A dermatoscopic image of a skin lesion.
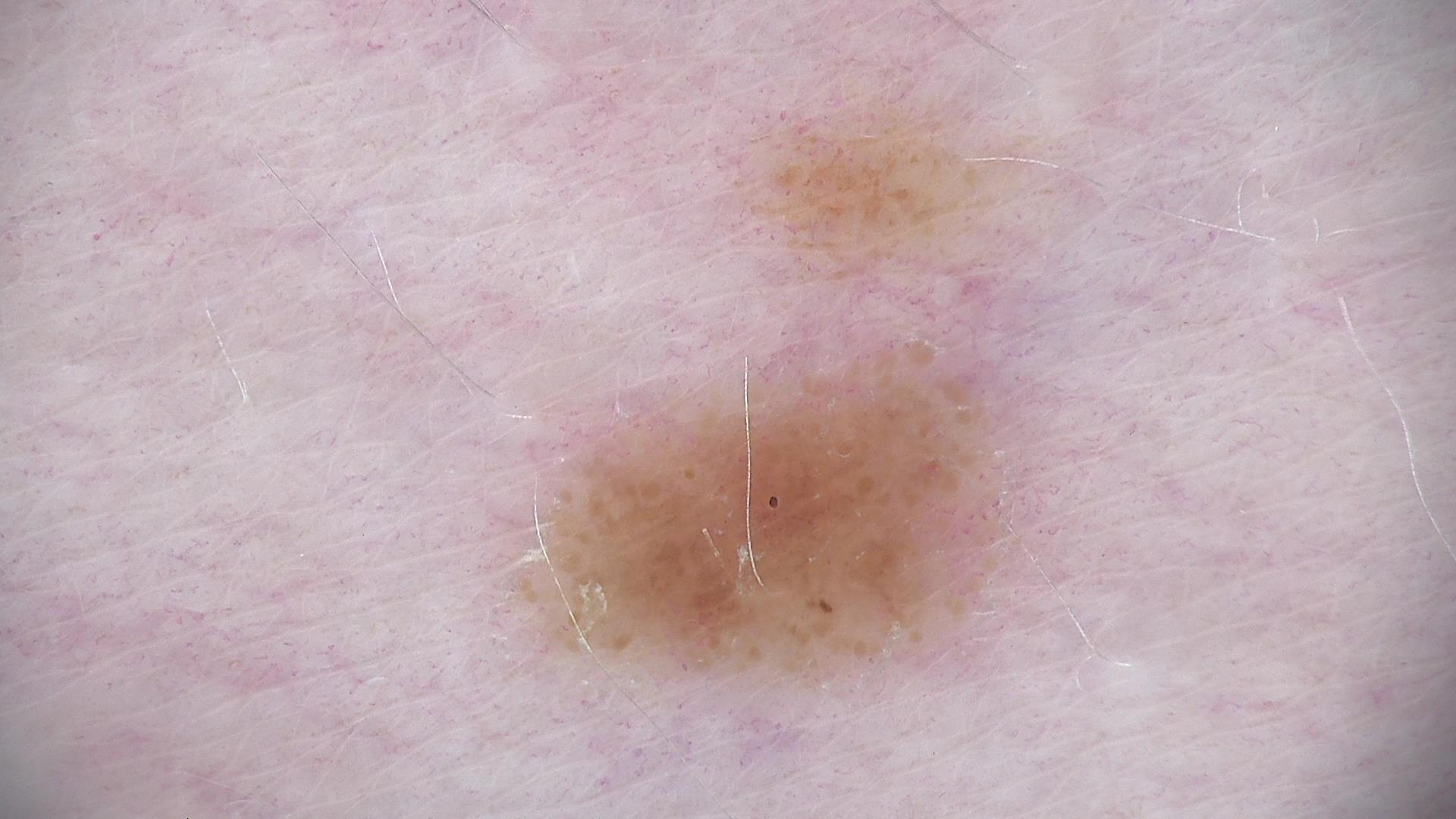Diagnosed as a benign lesion — a dysplastic junctional nevus.